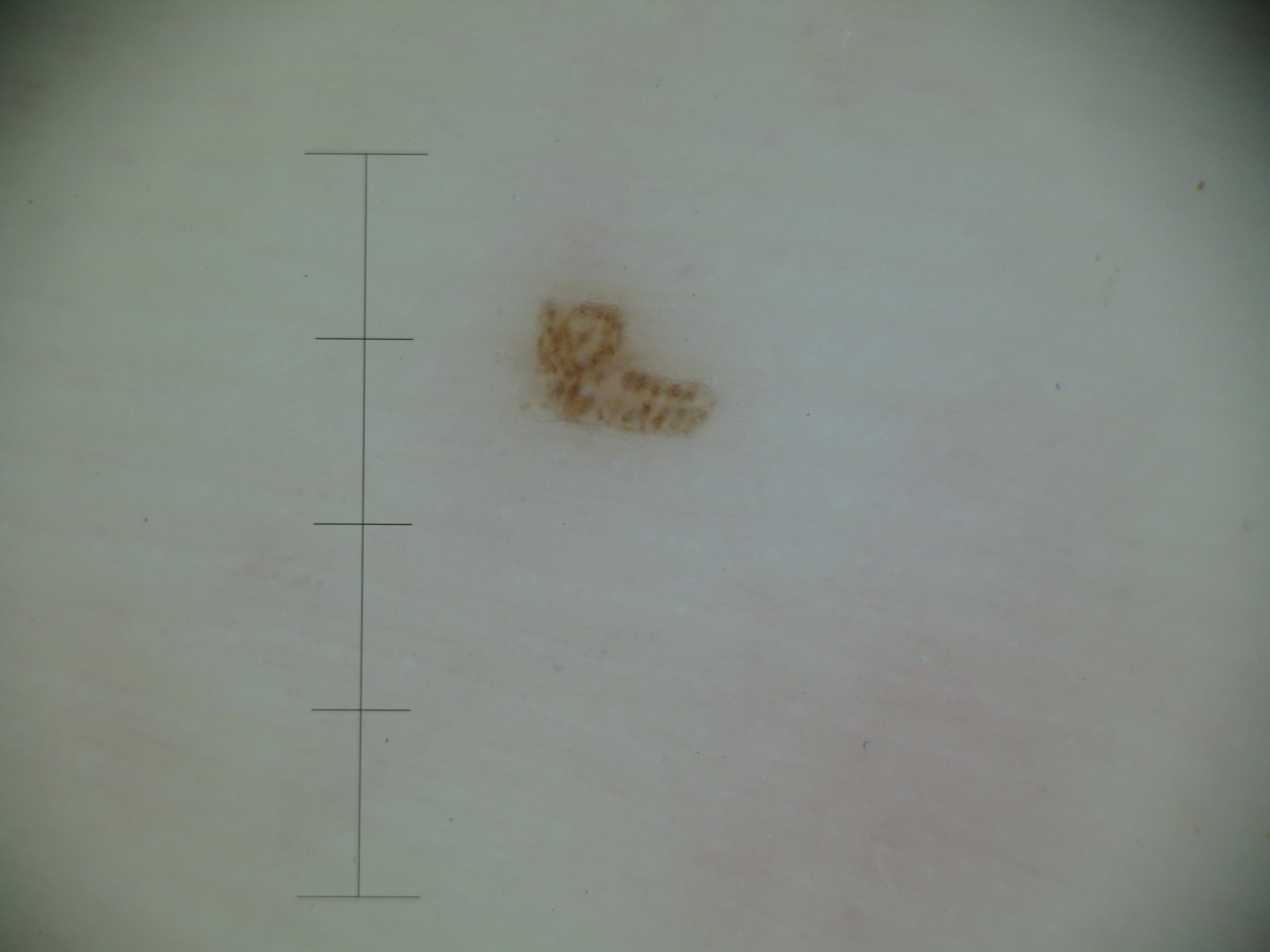Q: What is the diagnosis?
A: acral dysplastic junctional nevus (expert consensus)